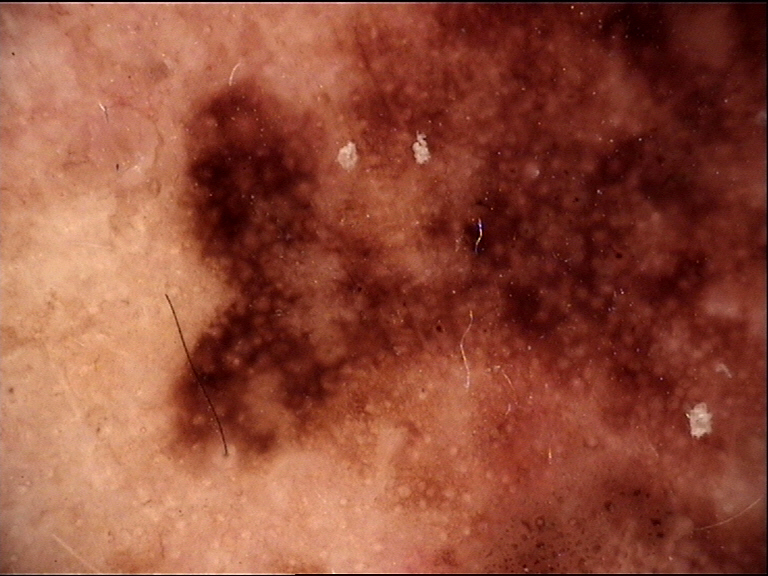The biopsy diagnosis was a lentigo maligna.